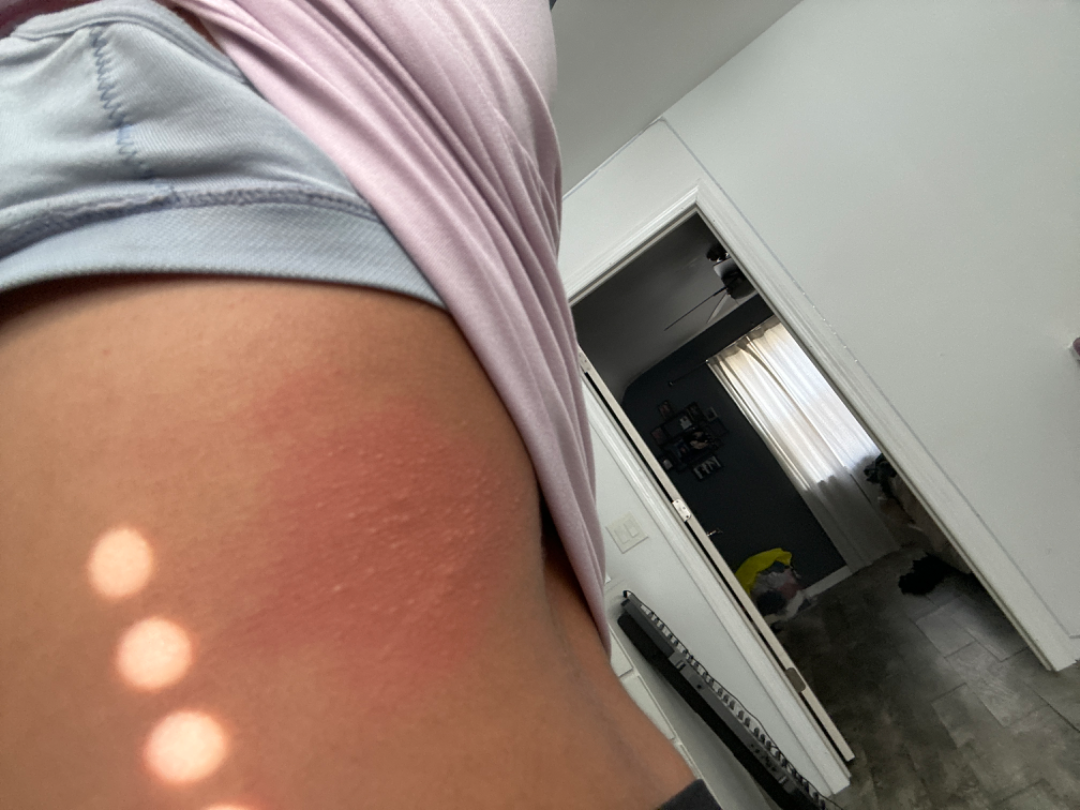The image was not sufficient for the reviewer to characterize the skin condition.
An image taken at a distance.